The patient indicates the lesion is raised or bumpy; located on the arm; an image taken at a distance; present for about one day: 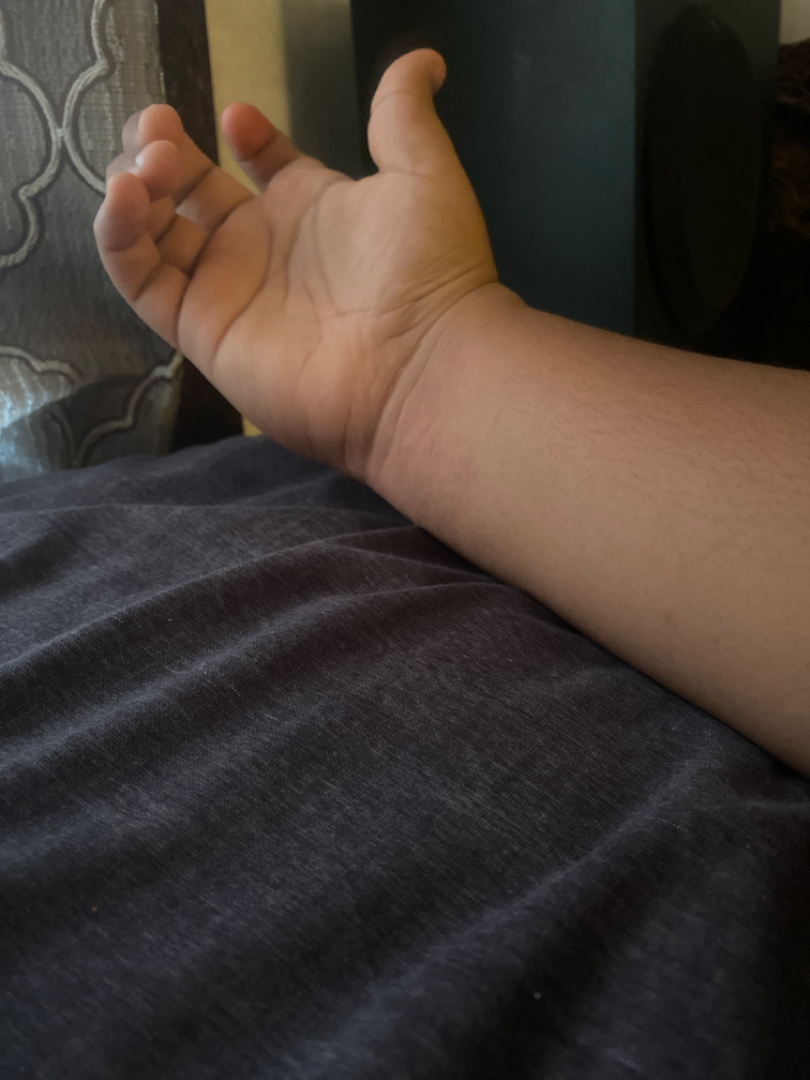The condition could not be reliably identified from the image.